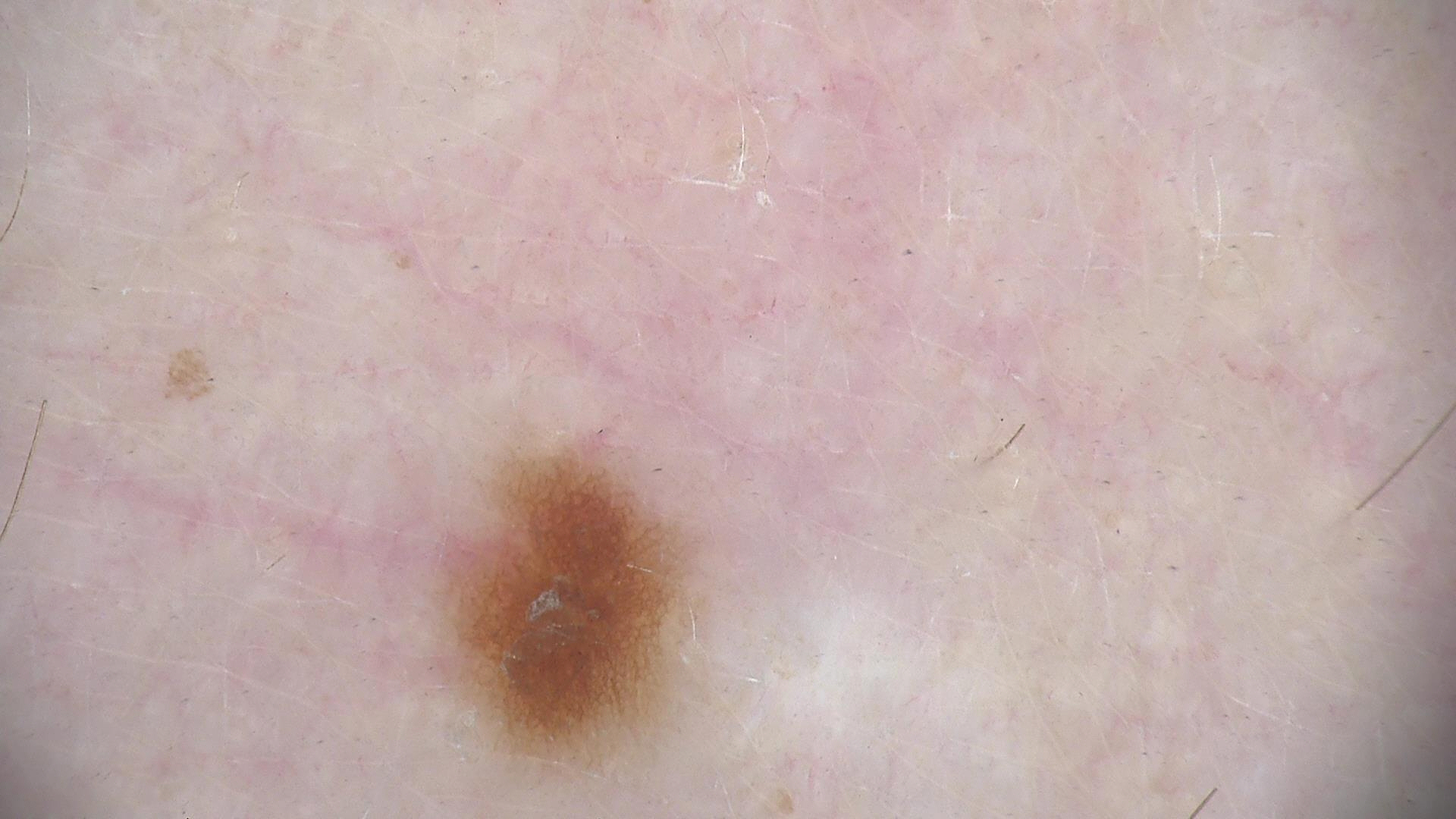A dermatoscopic image of a skin lesion. Diagnosed as a benign lesion — a dysplastic junctional nevus.